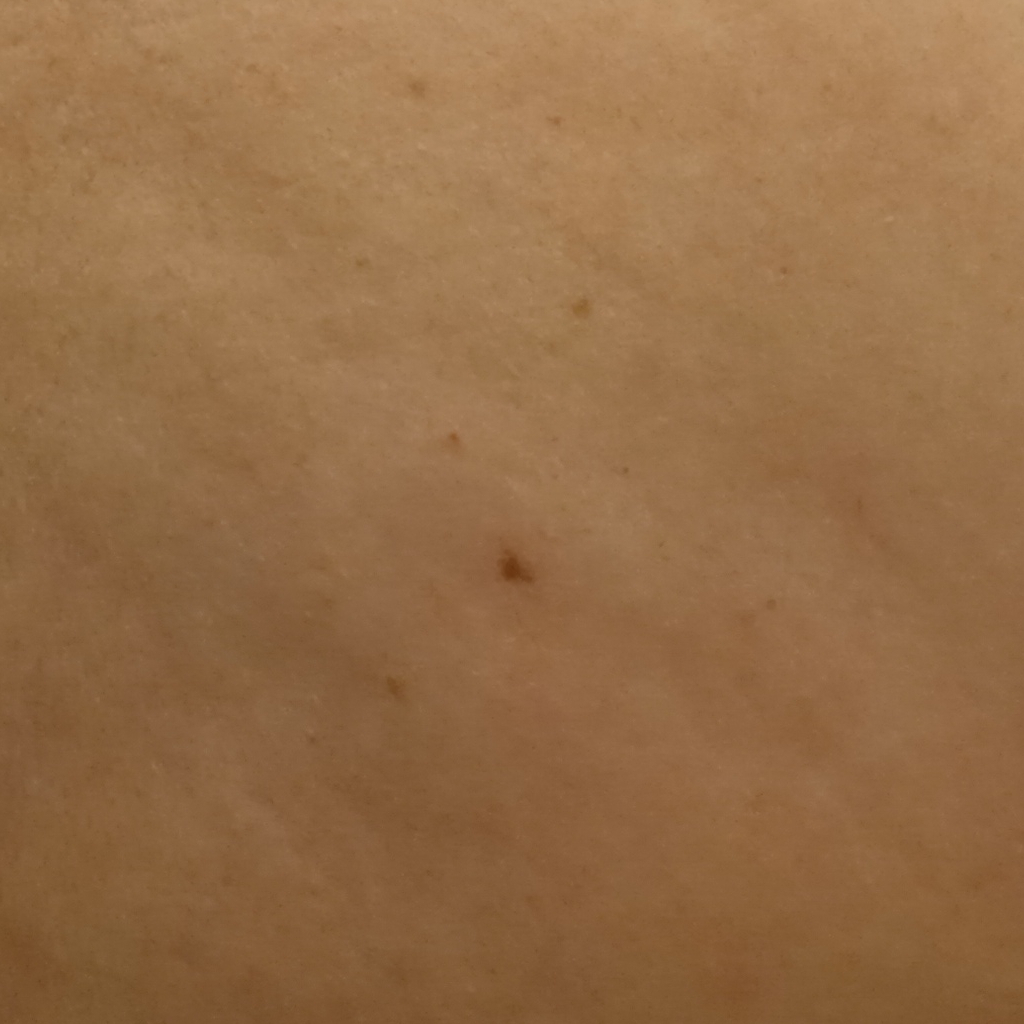- clinical context: research study (no referral diagnosis)
- patient: female, 48 years of age
- site: the back
- lesion size: 3.7 mm
- diagnostic label: melanocytic nevus (dermatologist consensus)